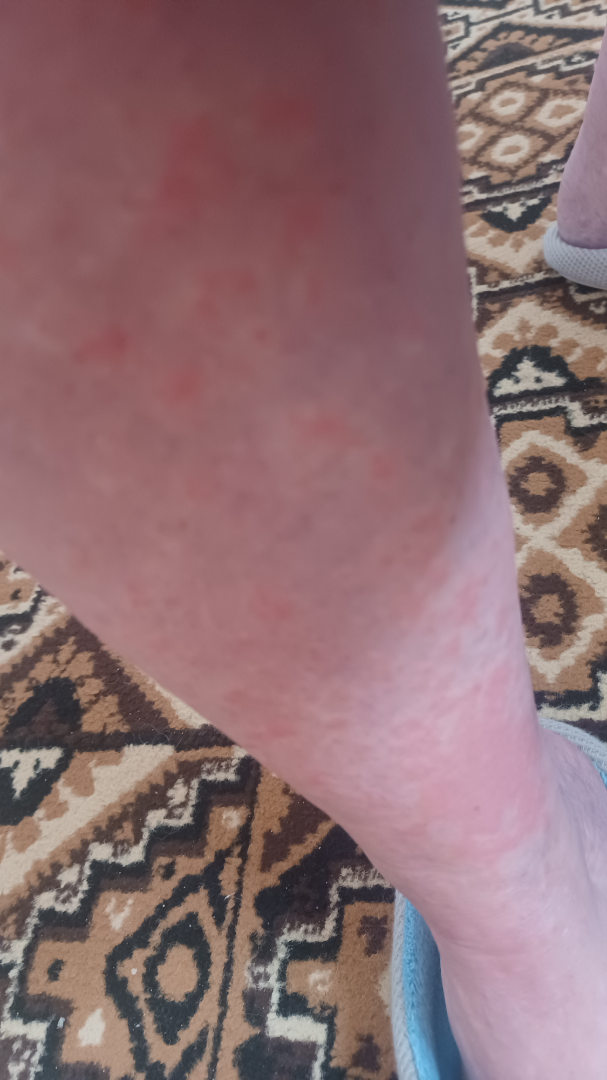| feature | finding |
|---|---|
| assessment | indeterminate |
| surface texture | raised or bumpy |
| image framing | at a distance |
| other reported symptoms | fatigue |
| self-categorized as | a rash |
| contributor | female, age 60–69 |
| location | front of the torso, arm and leg |
| onset | about one day |
| symptoms | bothersome appearance and burning |